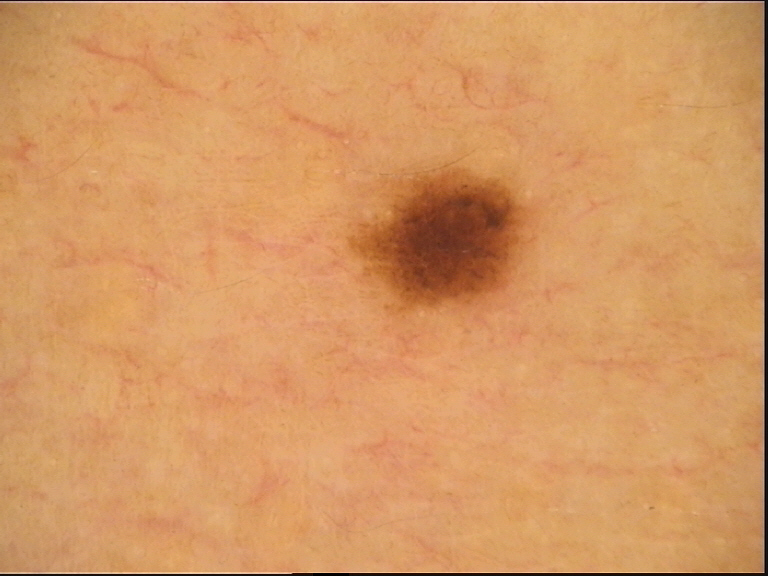– image type — dermoscopy
– label — dysplastic junctional nevus (expert consensus)